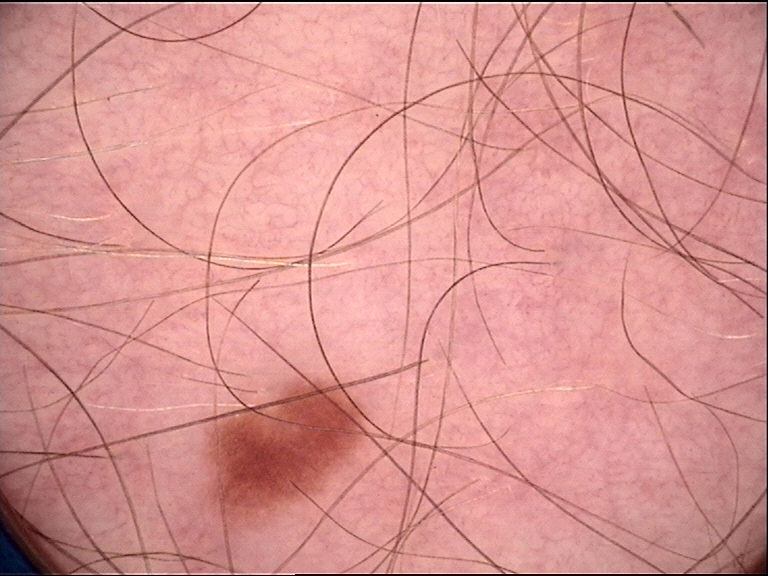class = dysplastic junctional nevus (expert consensus).